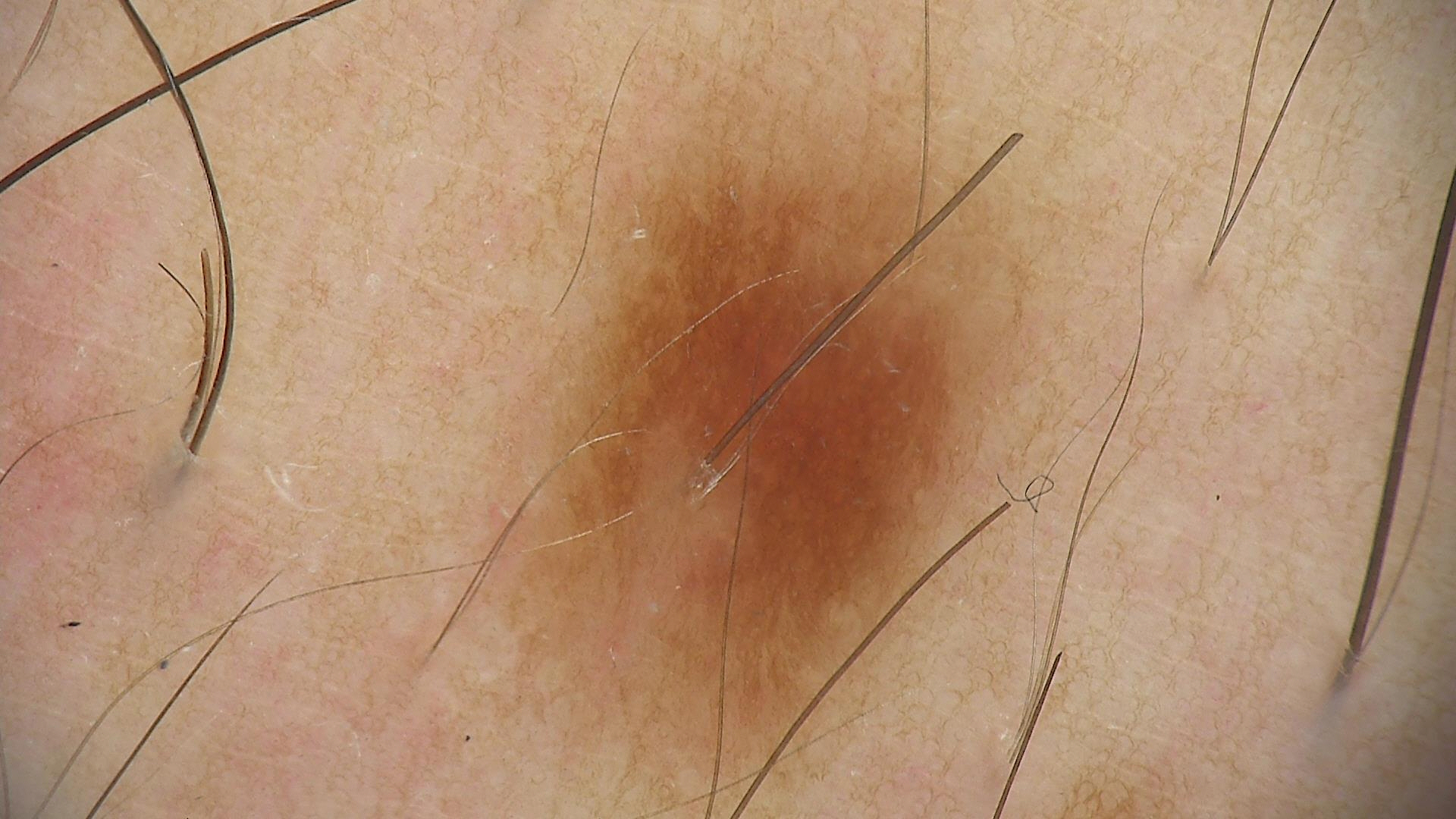diagnosis: dysplastic junctional nevus (expert consensus).